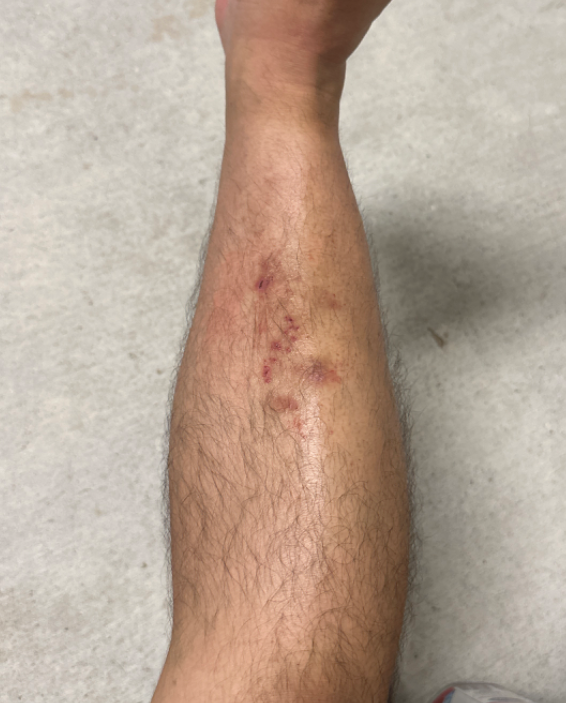Impression: Diagnostic features were not clearly distinguishable in this photograph. History: The leg is involved. The photo was captured at a distance.